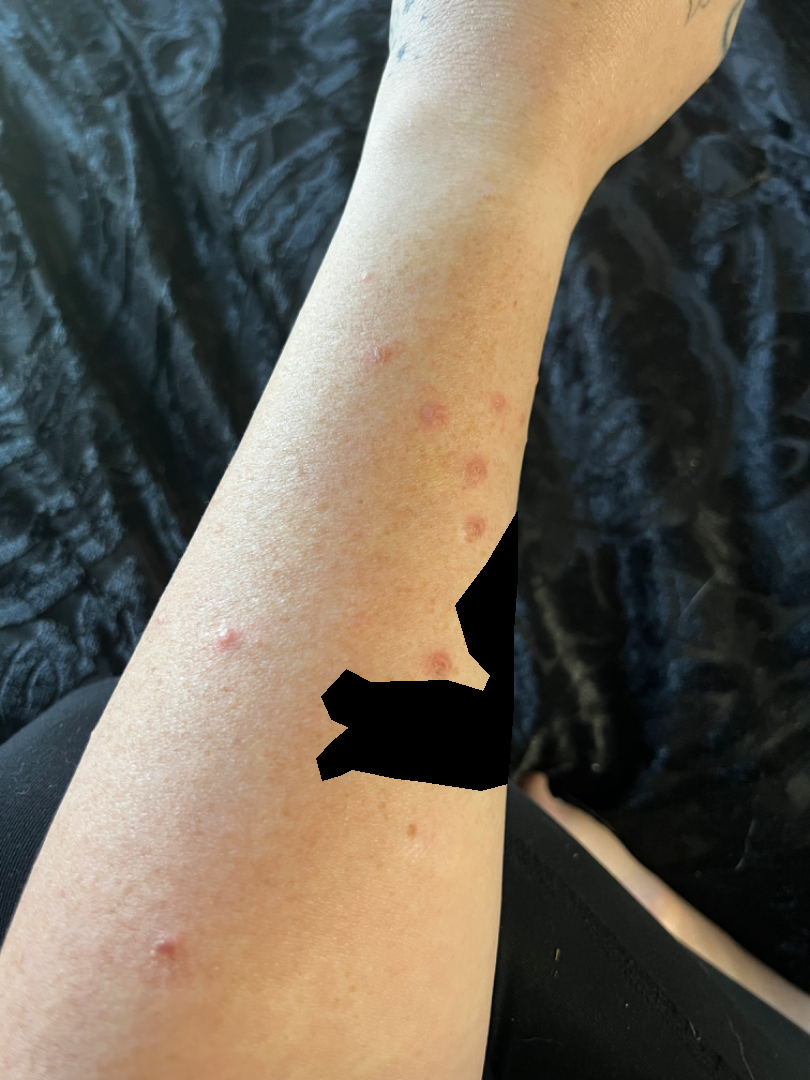Prurigo nodularis, Lymphomatoid papulosis and Pityriasis lichenoides were each considered, in no particular order.